A dermoscopic image of a skin lesion:
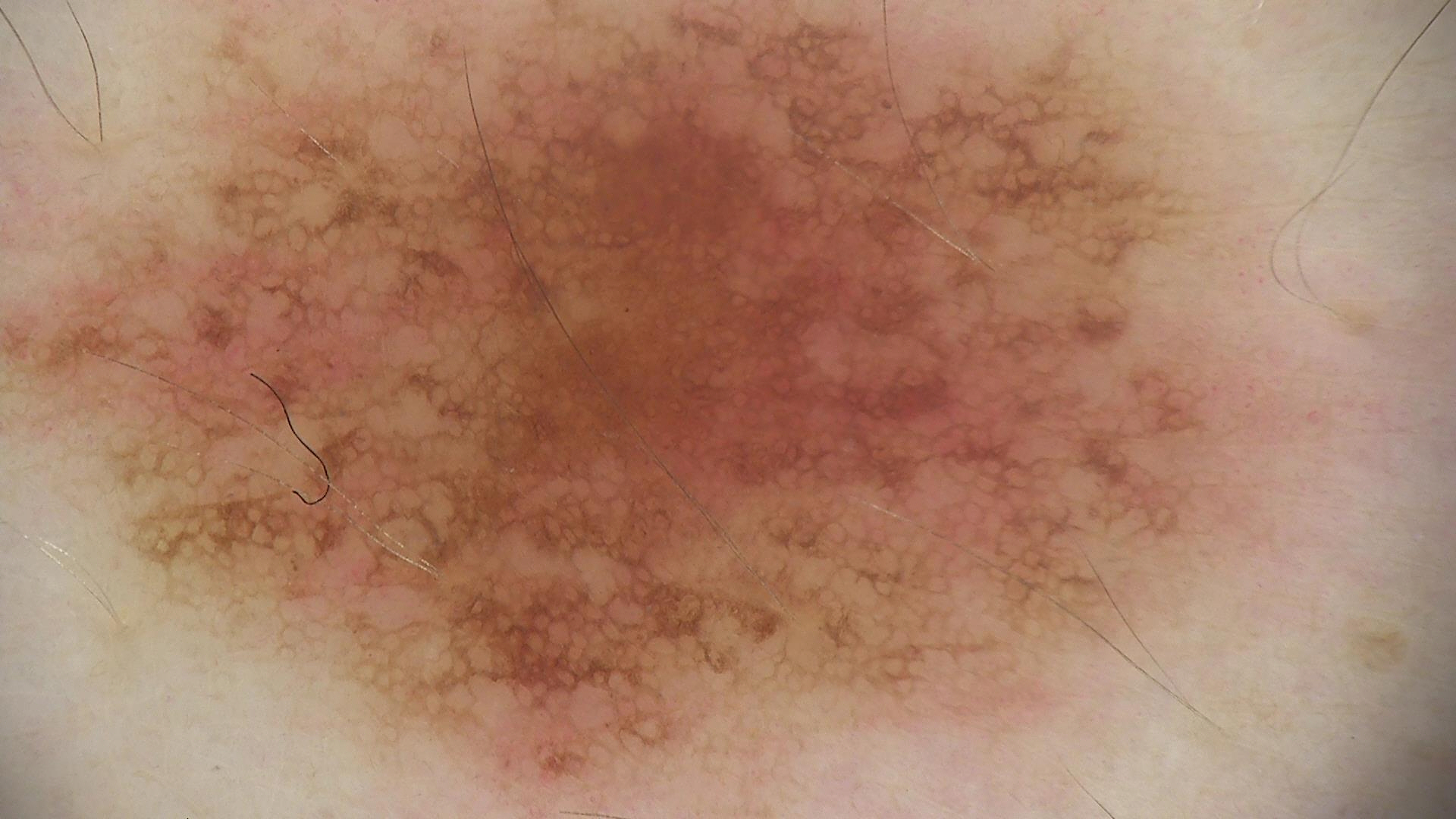Diagnosed as a dysplastic junctional nevus.